Close-up view · skin tone: non-clinician graders estimated Monk Skin Tone 3 or 5 (two reviewer pools disagreed) · the contributor is a male aged 30–39 · self-categorized by the patient as a rash · symptoms reported: itching · the condition has been present for less than one week · the affected area is the leg · the patient reports associated joint pain · the patient reports the lesion is raised or bumpy: 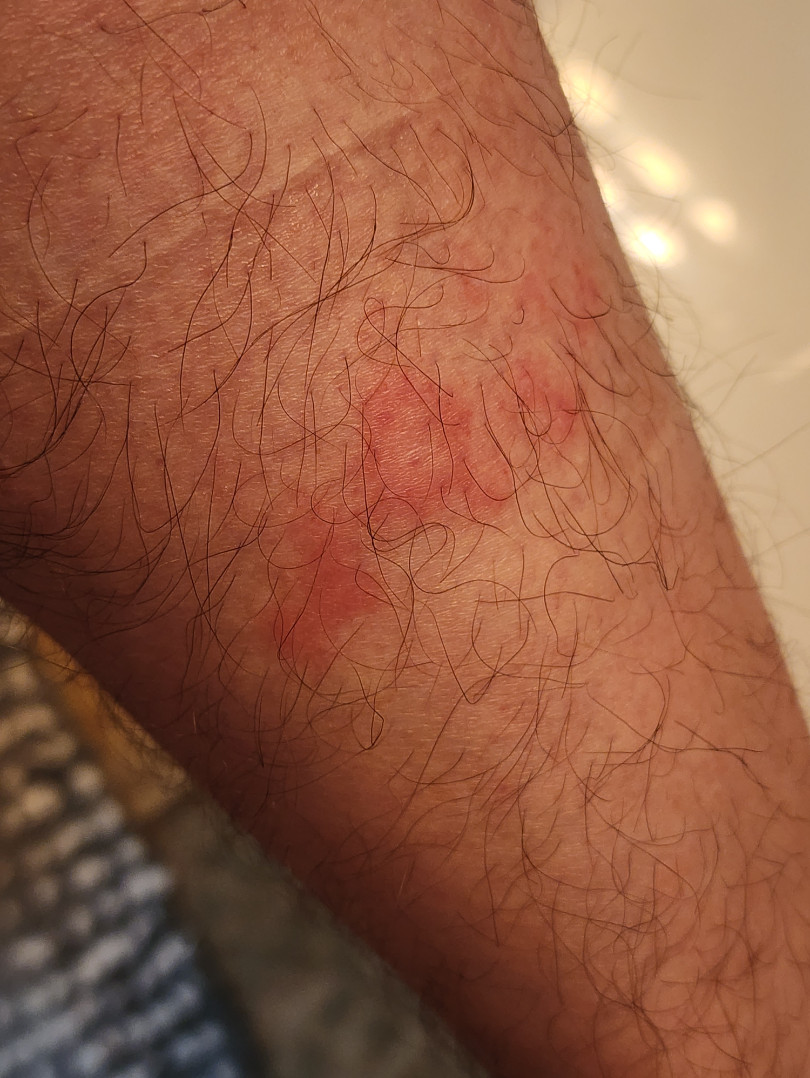Impression: On dermatologist assessment of the image: Allergic Contact Dermatitis and Irritant Contact Dermatitis were considered with similar weight.